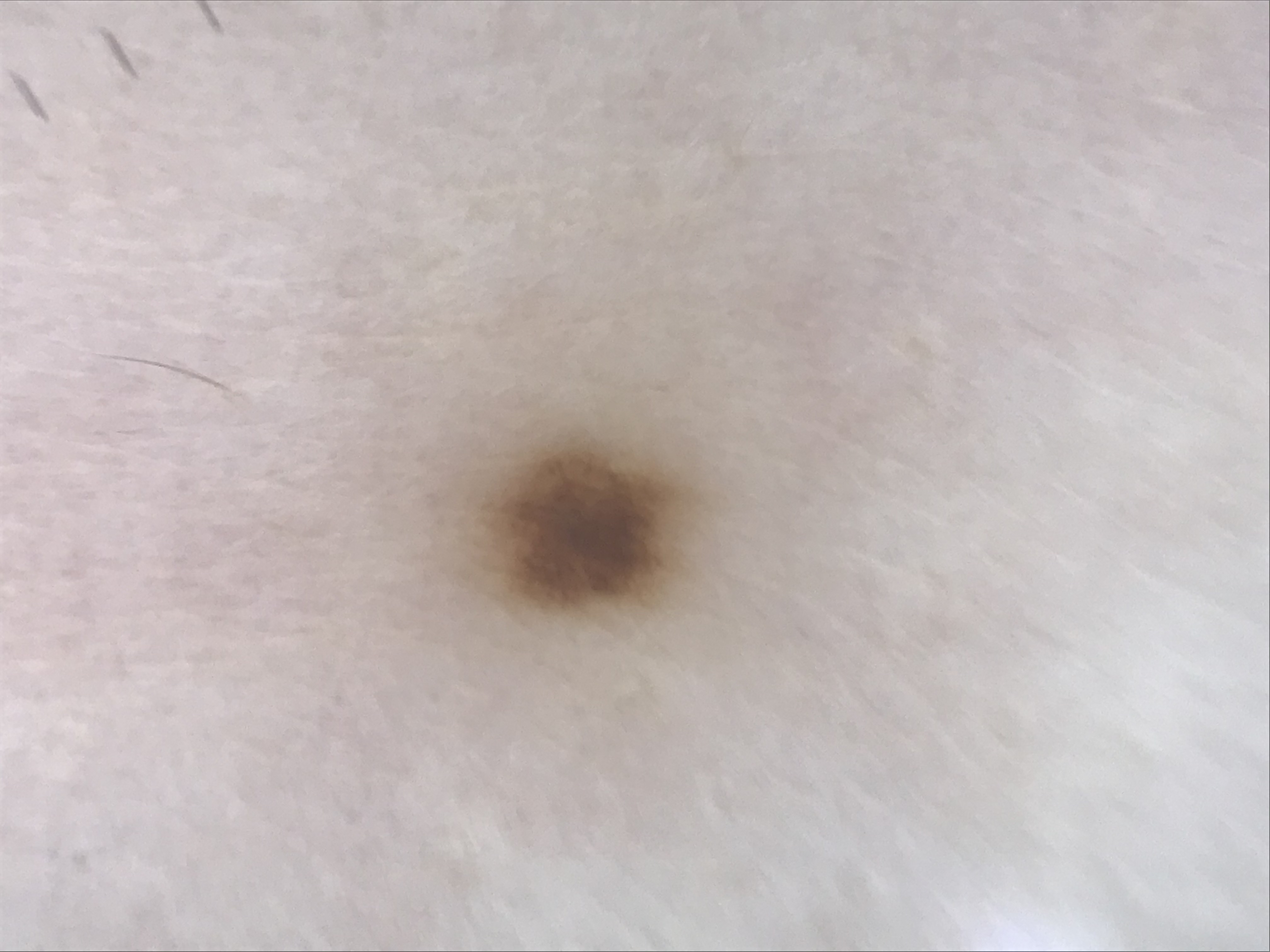Impression: Labeled as a junctional nevus.